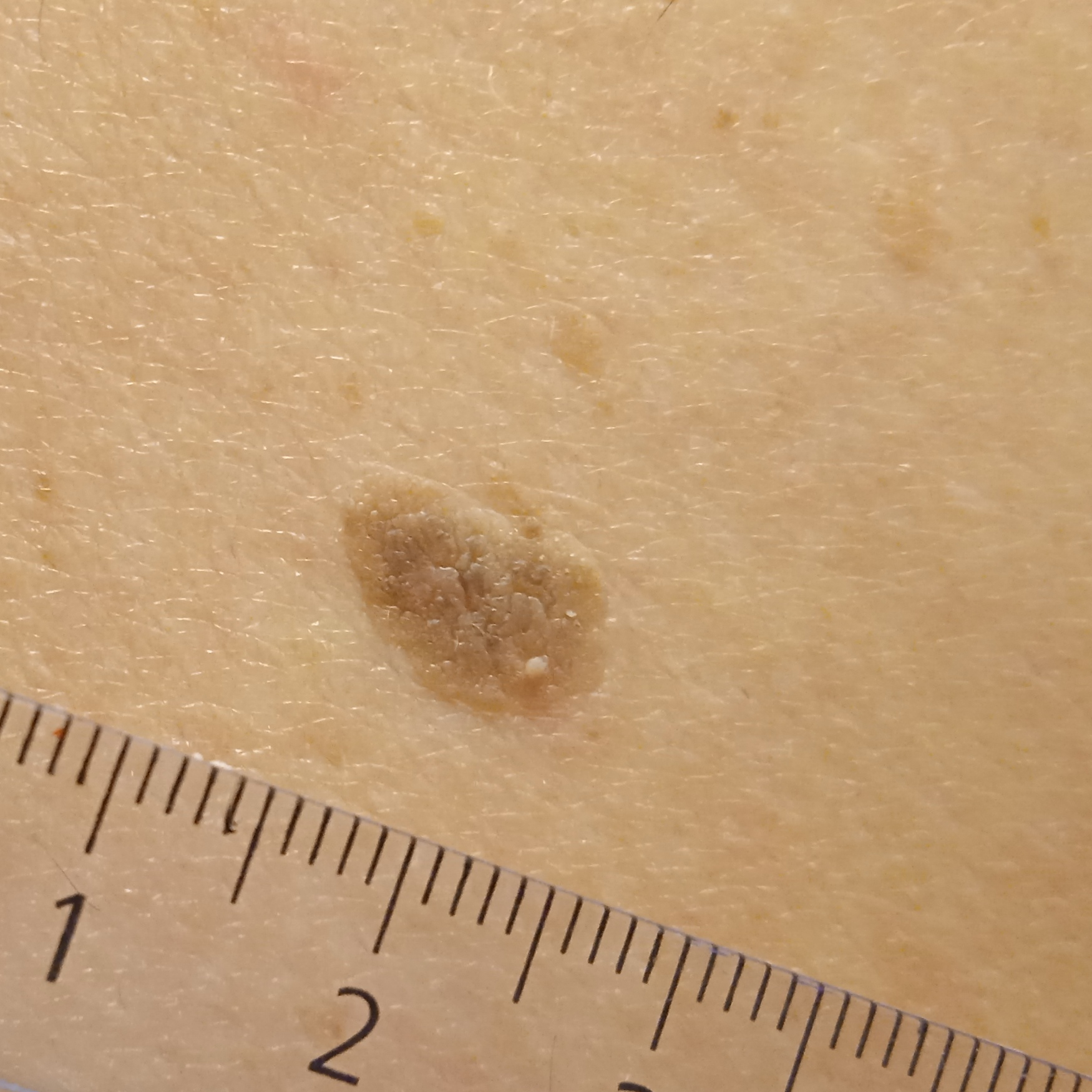Findings:
- imaging — clinical photograph
- sun reaction — skin tans without first burning
- nevus count — few melanocytic nevi overall
- referral — clinical suspicion of seborrheic keratosis
- location — the back
- size — 11.4 mm
- assessment — seborrheic keratosis (dermatologist consensus)